The photograph was taken at a distance, the lesion involves the back of the hand: 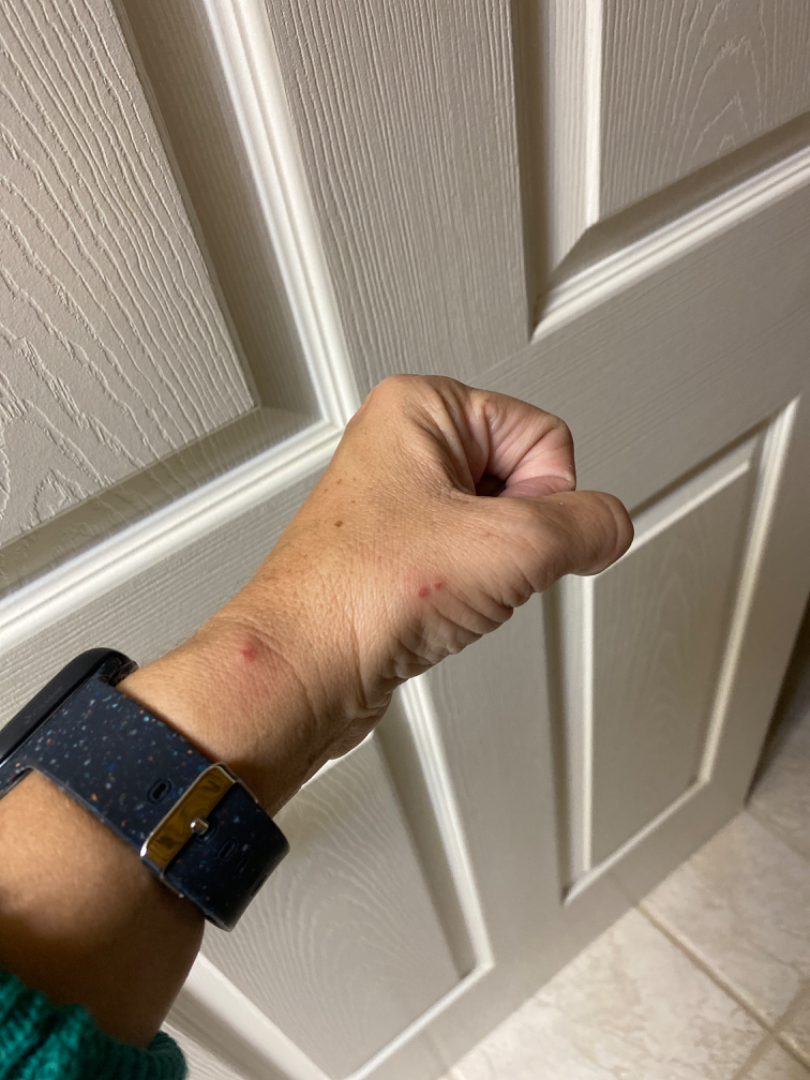Notes:
– history: one to four weeks
– lesion texture: raised or bumpy
– skin tone: Fitzpatrick skin type III; non-clinician graders estimated MST 2 or 3
– associated systemic symptoms: none reported
– differential: Insect Bite (leading); Eczema (possible); Allergic Contact Dermatitis (possible)